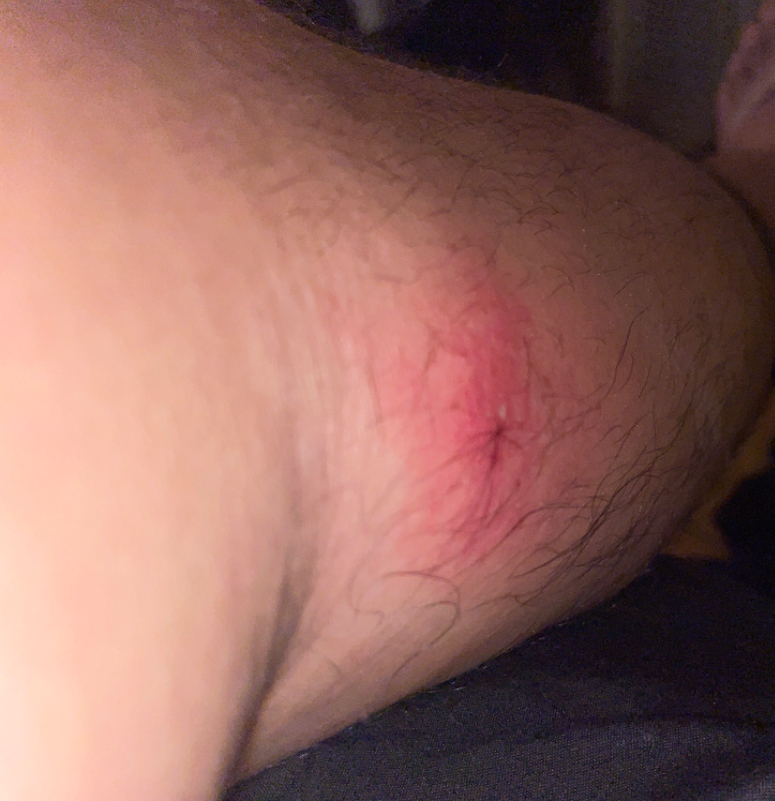The contributor is 18–29, male.
The leg is involved.
This image was taken at an angle.
The favored diagnosis is Cellulitis.